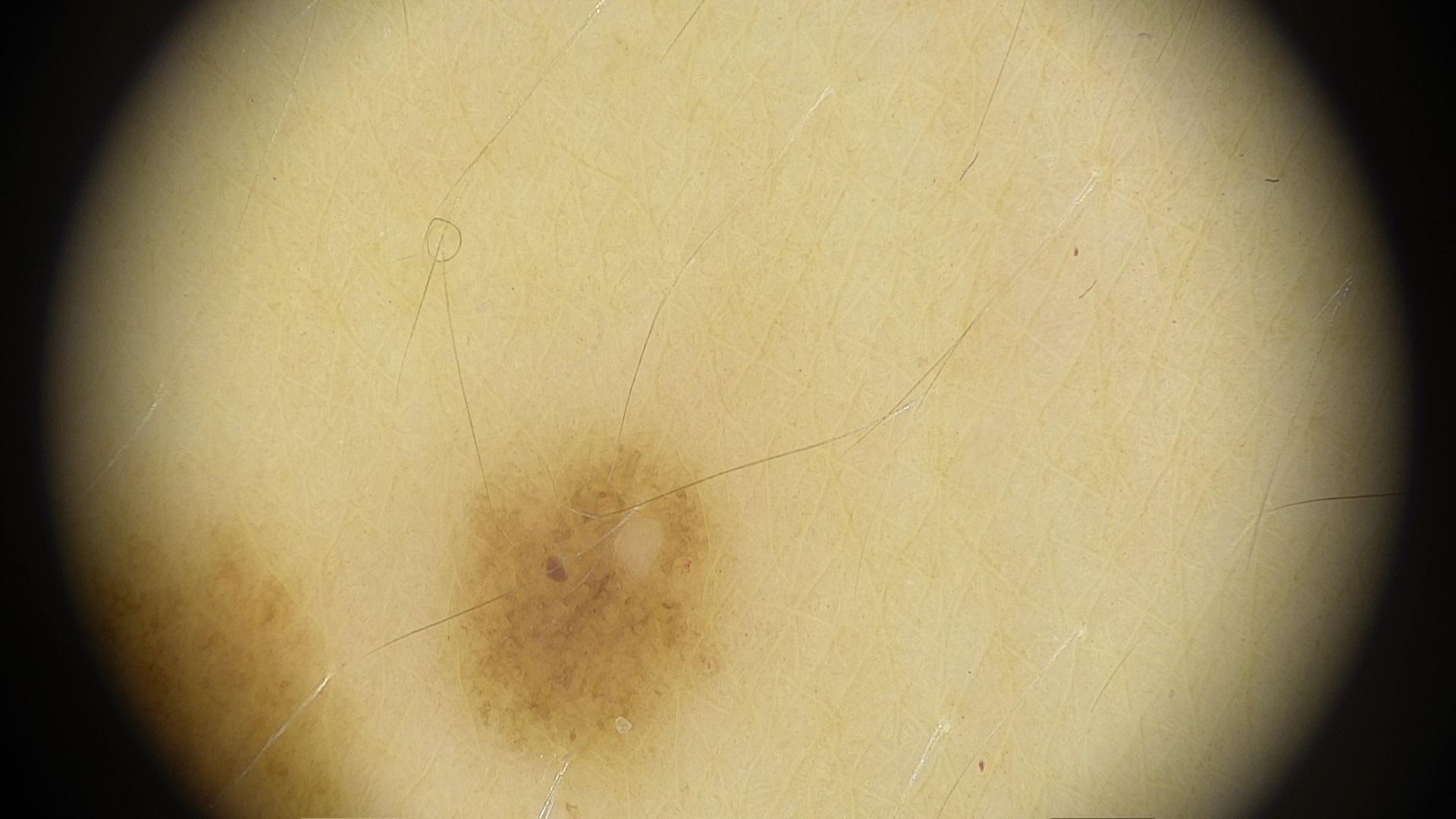Contact-polarized dermoscopy of a skin lesion. The lesion involves the anterior trunk. Consistent with a nevus.